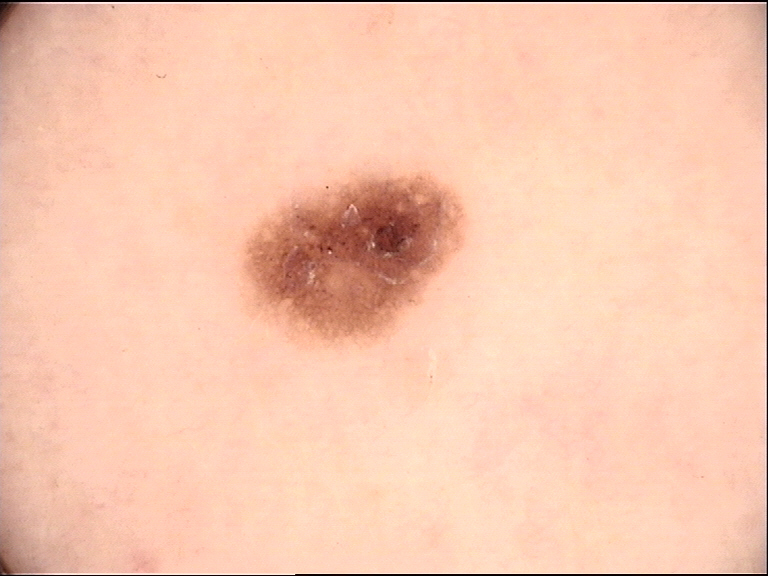A dermoscopic close-up of a skin lesion. Consistent with a dysplastic junctional nevus.